A male subject, aged approximately 20. Dermoscopy of a skin lesion.
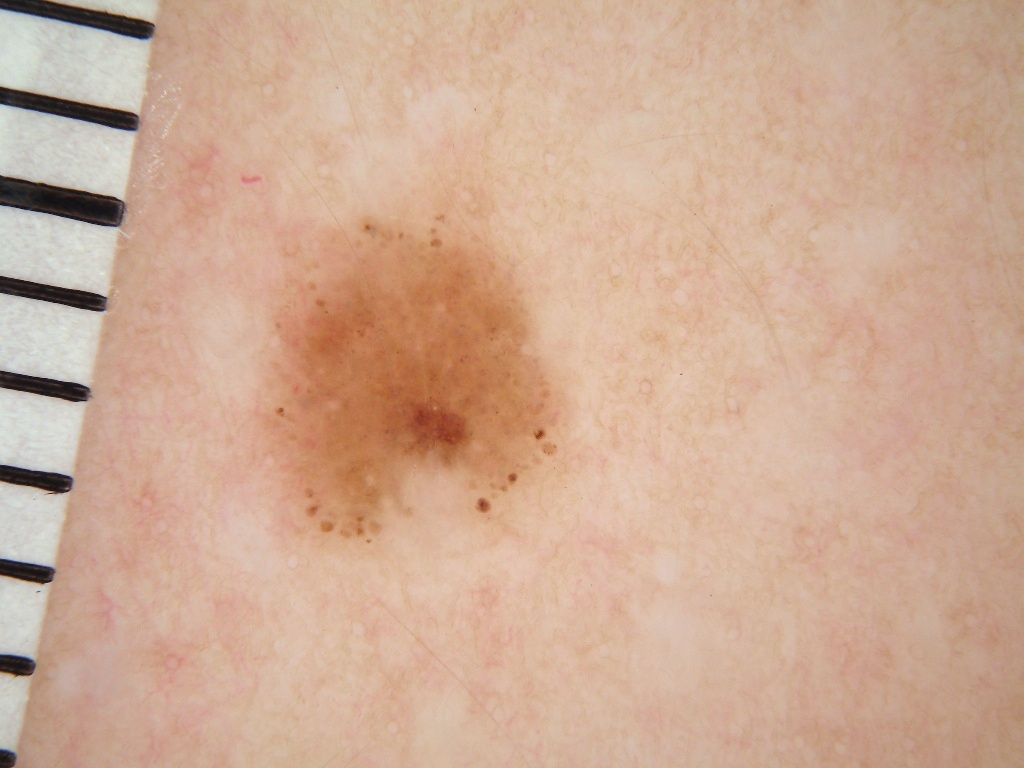Dermoscopically, the lesion shows globules; no negative network, milia-like cysts, pigment network, or streaks. The lesion spans 233, 191, 581, 566. Expert review diagnosed this as a melanocytic nevus, a benign skin lesion.